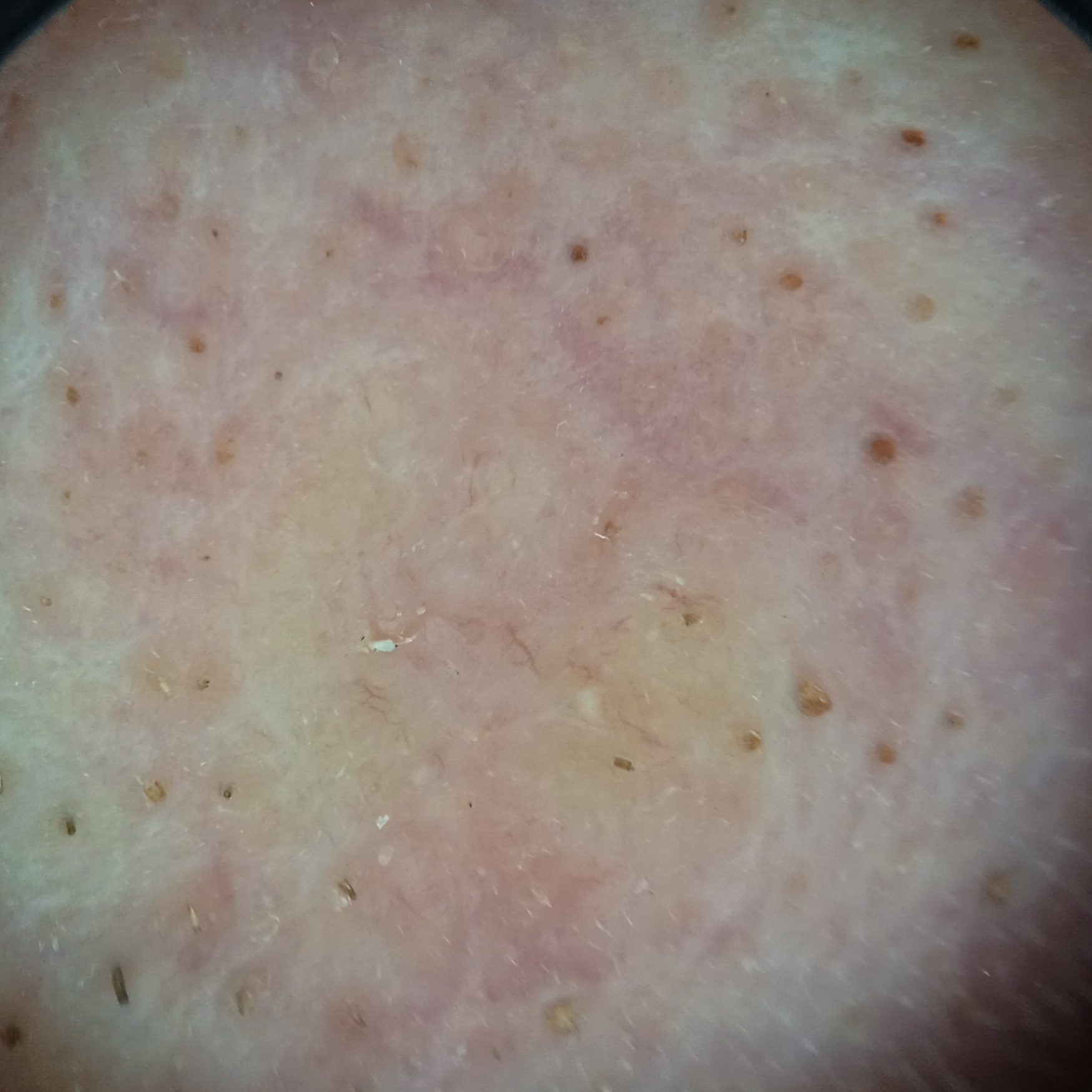Dermoscopy of a skin lesion. Referred for assessment of suspected basal cell carcinoma. Located on the face. The lesion measures approximately 8.5 mm. On biopsy, the diagnosis was a basal cell carcinoma, following excision, with a measured thickness of 1.7 mm.